Dermoscopy of a skin lesion. The patient is female: 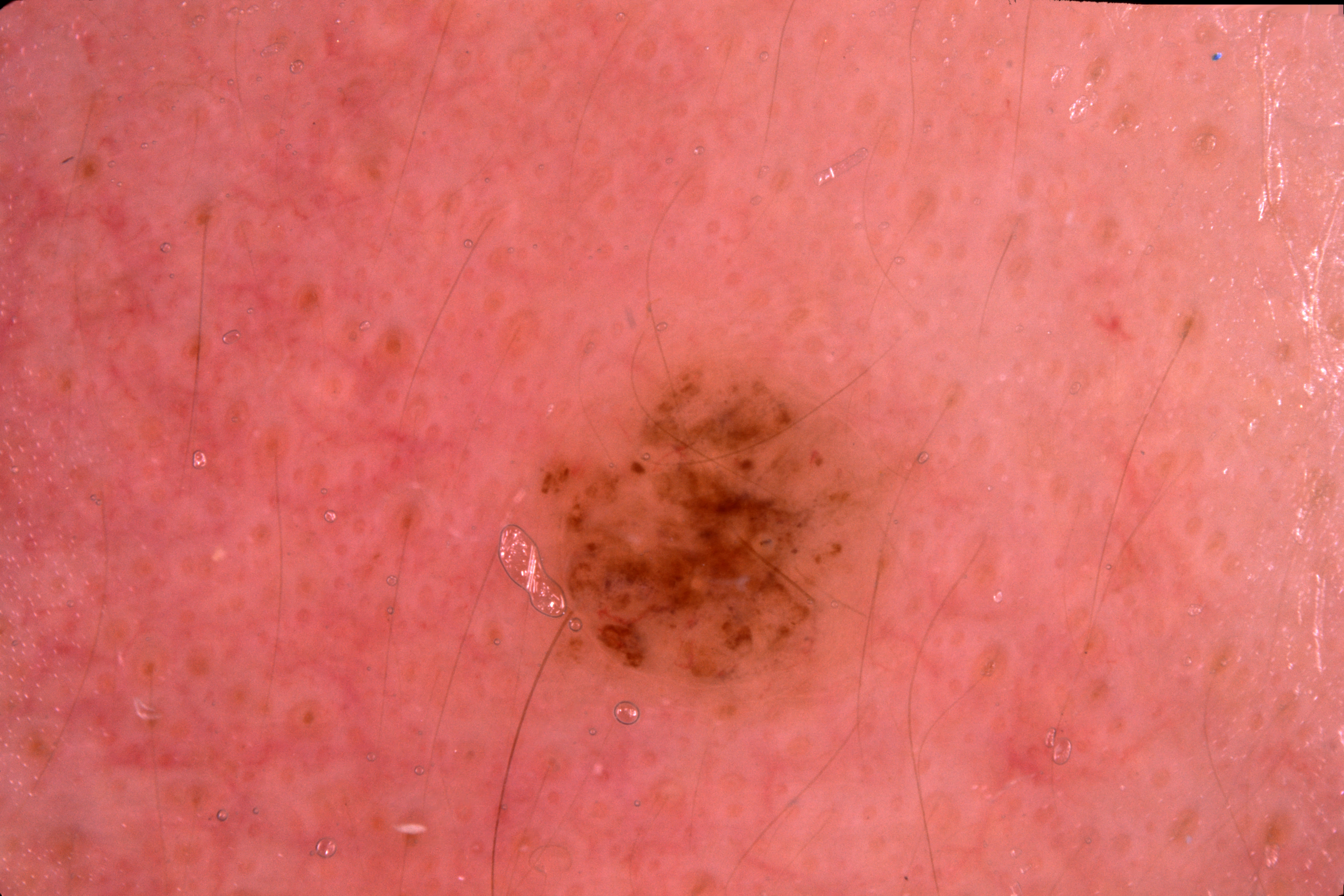{
  "lesion_location": {
    "bbox_xyxy": [
      517,
      353,
      909,
      728
    ]
  },
  "dermoscopic_features": {
    "present": [],
    "absent": [
      "streaks",
      "negative network",
      "milia-like cysts",
      "pigment network"
    ]
  },
  "lesion_extent": {
    "approx_field_fraction_pct": 10
  },
  "diagnosis": {
    "name": "melanocytic nevus",
    "malignancy": "benign",
    "lineage": "melanocytic",
    "provenance": "clinical"
  }
}